A close-up photograph.
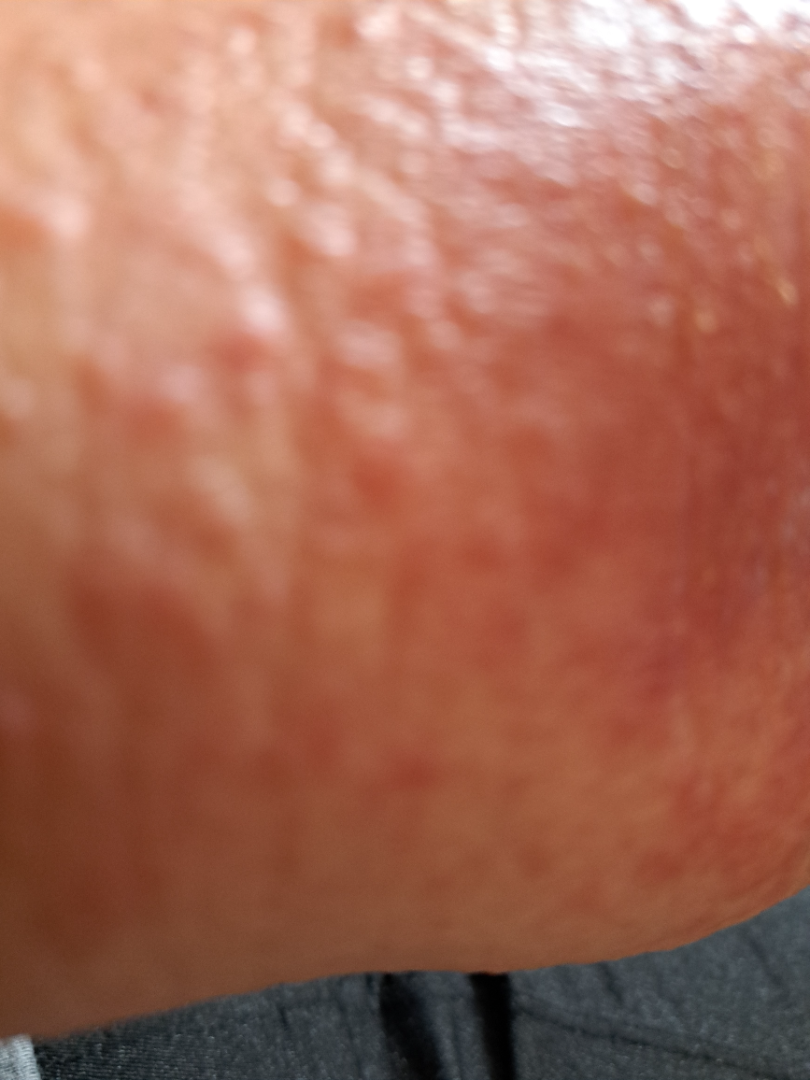The skin condition could not be confidently assessed from this image.